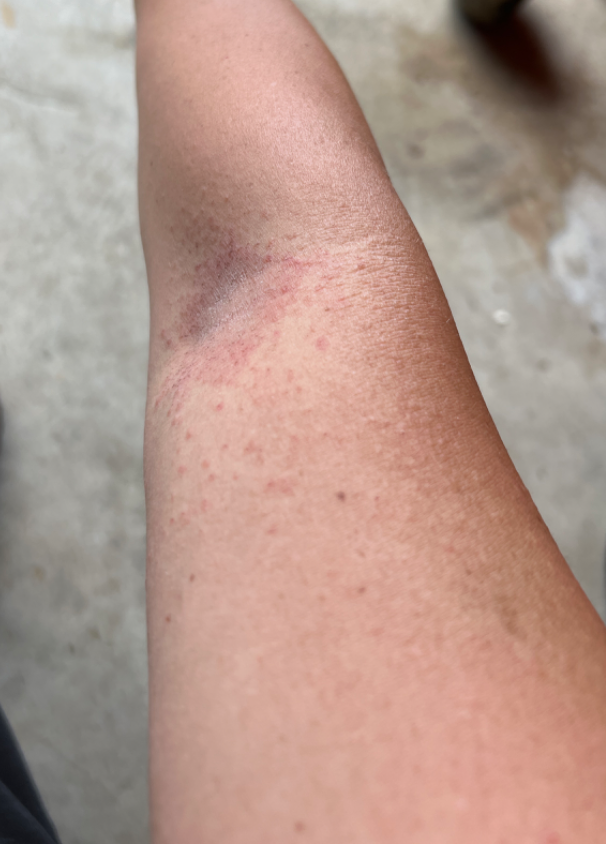Q: What is the affected area?
A: arm
Q: Who is the patient?
A: female, age 30–39
Q: How was the photo taken?
A: at a distance
Q: What conditions are considered?
A: single-reviewer assessment: favoring Eczema; possibly Allergic Contact Dermatitis; less likely is Tinea